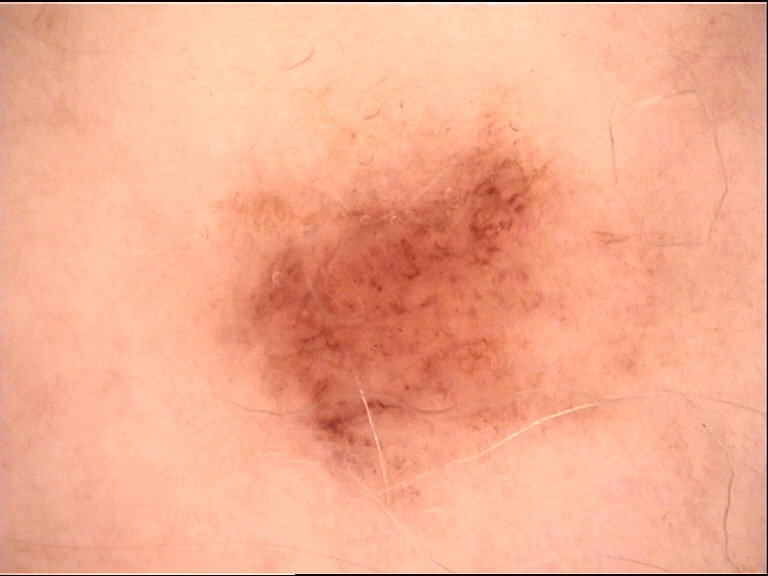Q: What kind of image is this?
A: dermoscopy
Q: What is this lesion?
A: dysplastic junctional nevus (expert consensus)